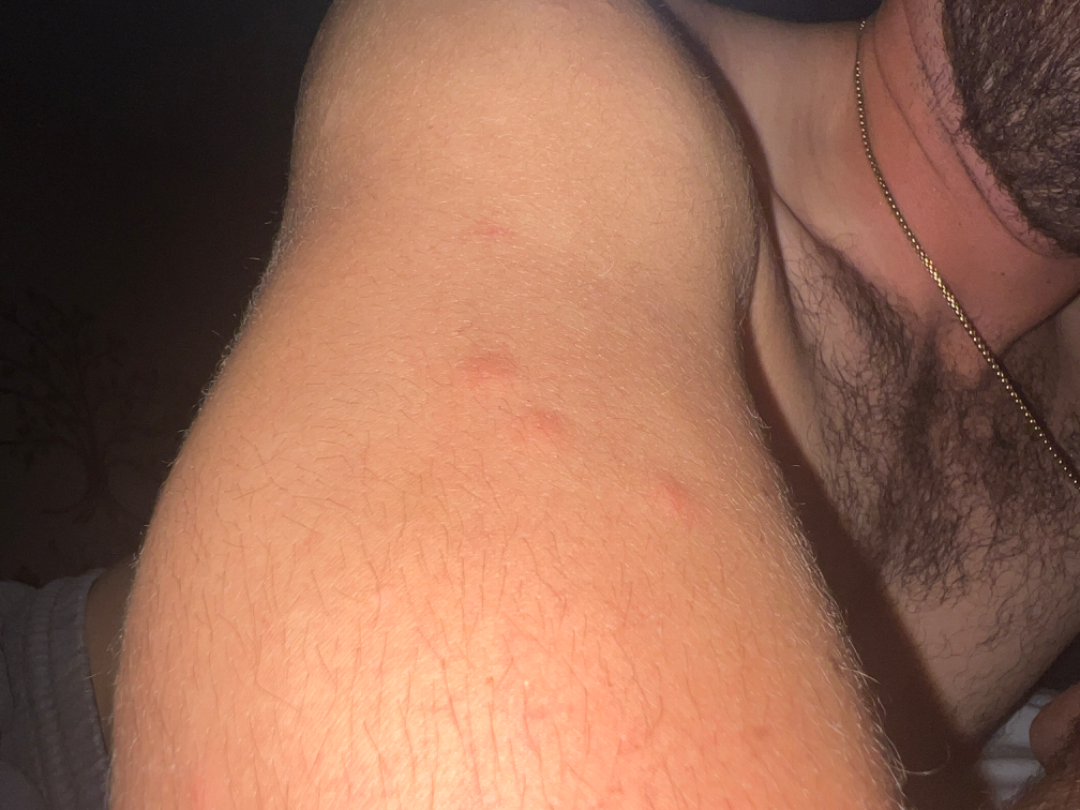History:
The condition has been present for less than one week. The subject is 18–29, male. An image taken at an angle. The lesion involves the arm. Self-categorized by the patient as a rash.
Impression:
Three dermatologists independently reviewed the case: the favored diagnosis is Insect Bite; less likely is Allergic Contact Dermatitis; a remote consideration is Folliculitis; lower on the differential is Urticaria.